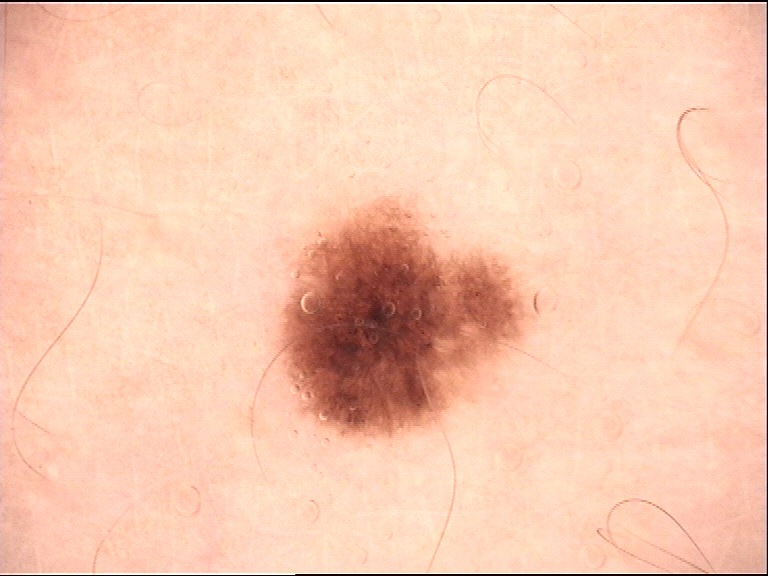Findings: A dermoscopic photograph of a skin lesion. Conclusion: Classified as a dysplastic junctional nevus.